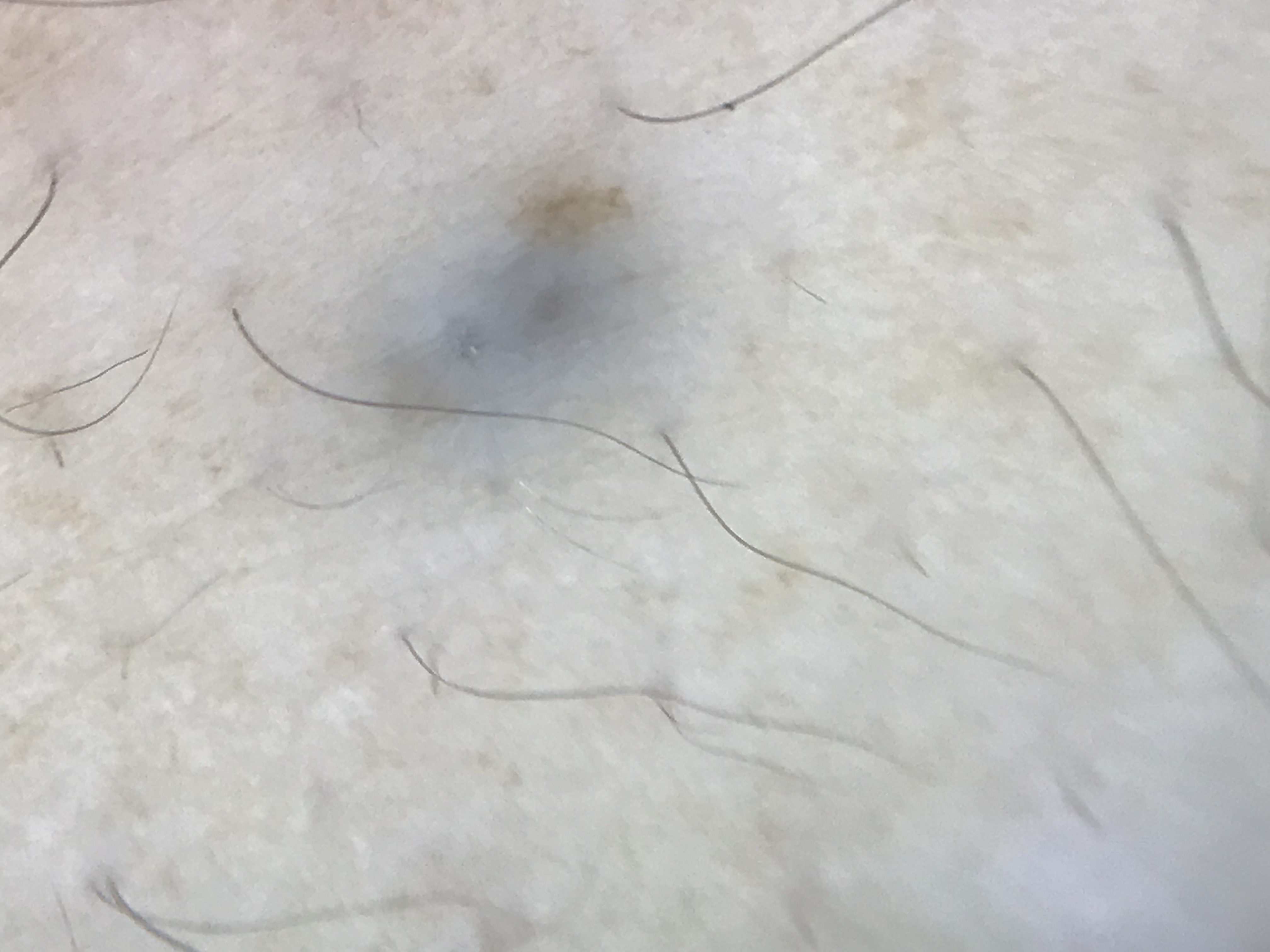{
  "lesion_type": {
    "main_class": "banal",
    "pattern": "dermal"
  },
  "diagnosis": {
    "name": "blue nevus",
    "code": "bdb",
    "malignancy": "benign",
    "super_class": "melanocytic",
    "confirmation": "expert consensus"
  }
}